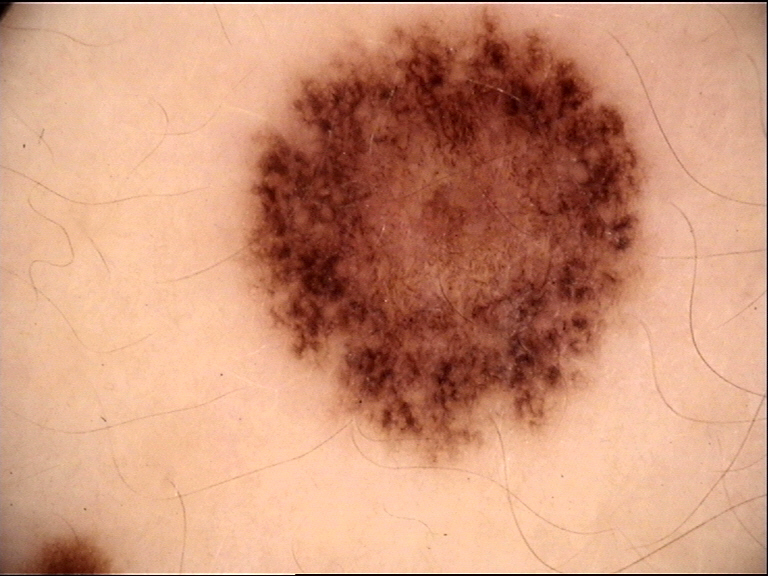image: dermoscopy
class: dysplastic compound nevus (expert consensus)